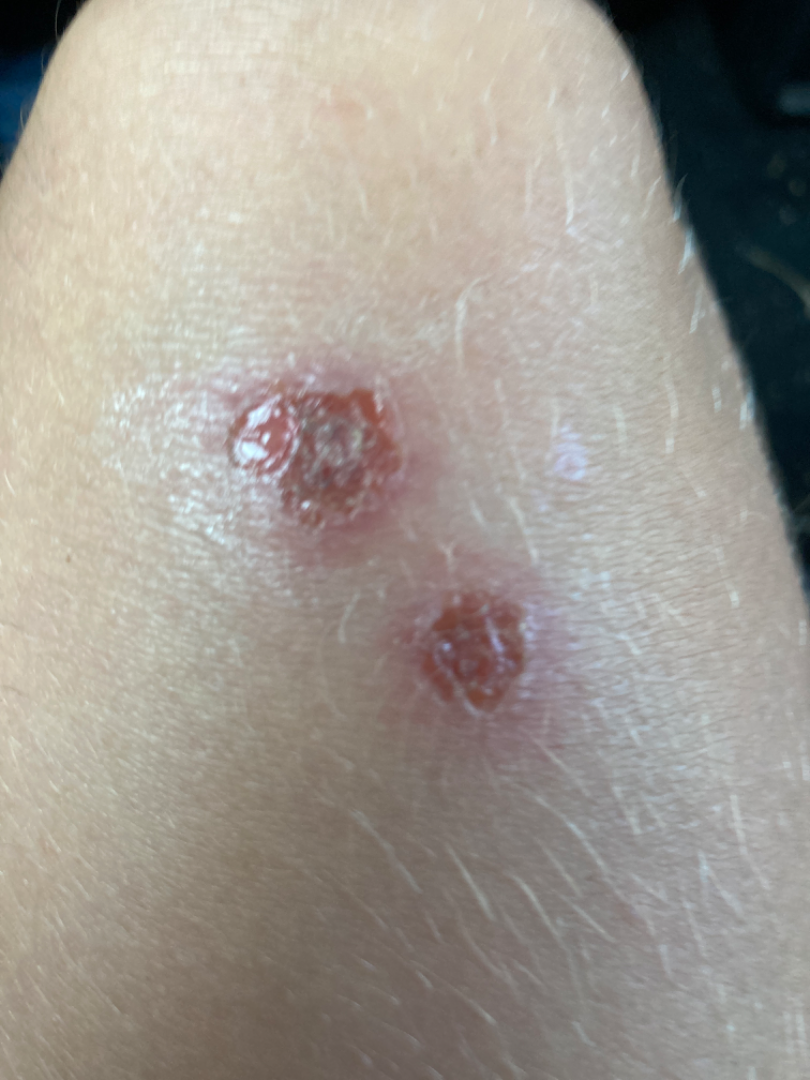The reviewing clinician's impression was: Ecthyma and Impetigo were each considered, in no particular order.